The contributor is 18–29, female · located on the top or side of the foot · an image taken at an angle — 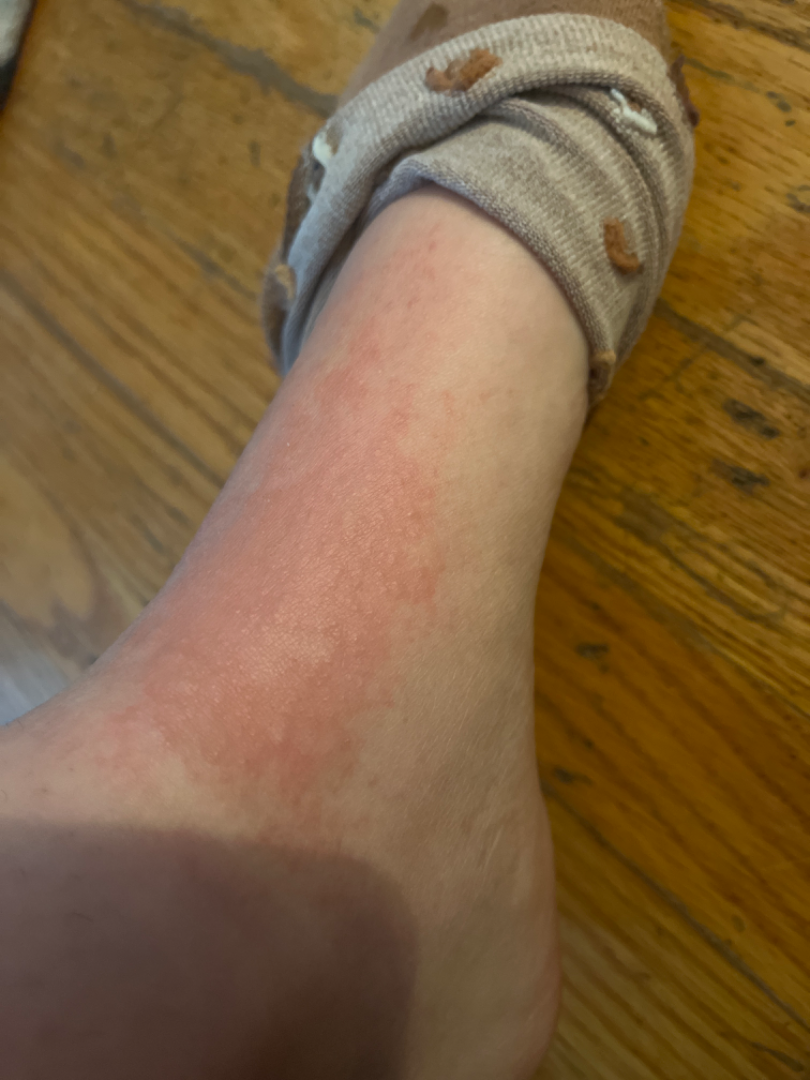Patient information: The condition has been present for about one day. The contributor notes the lesion is raised or bumpy. Symptoms reported: itching and bothersome appearance. Self-categorized by the patient as a rash. Review: On remote review of the image, Allergic Contact Dermatitis (most likely); Irritant Contact Dermatitis (considered); Stasis Dermatitis (unlikely).